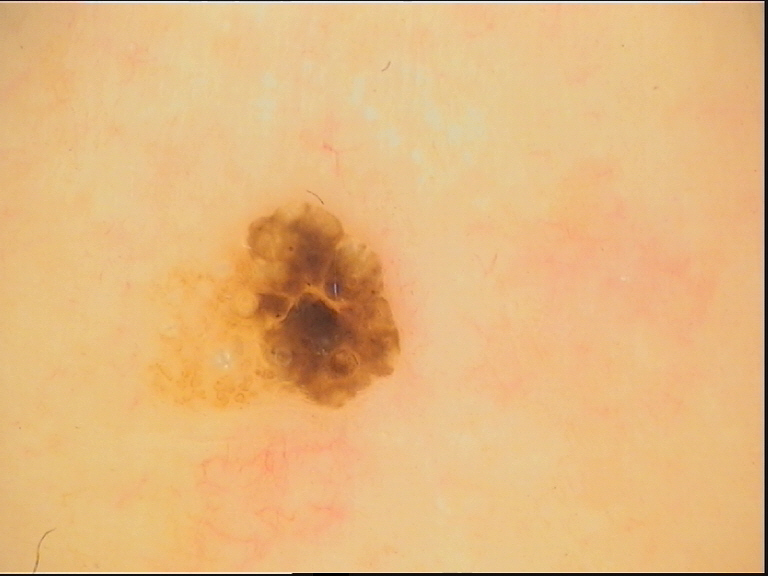Findings: A skin lesion imaged with a dermatoscope. Impression: The diagnosis was a keratinocytic lesion — a seborrheic keratosis.